Reported duration is one to three months; skin tone: Fitzpatrick IV; the leg is involved; texture is reported as raised or bumpy; the photo was captured at an angle; the patient described the issue as a rash; no relevant systemic symptoms: 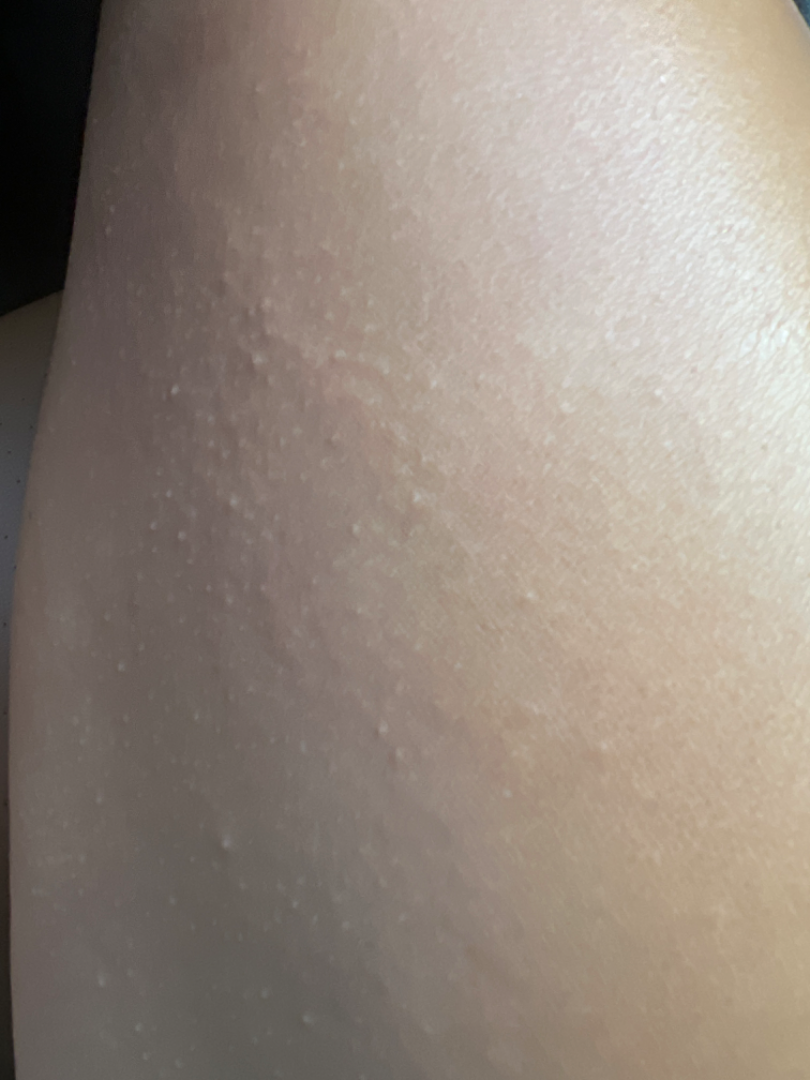On photographic review by a dermatologist: the primary impression is Keratosis pilaris; possibly Lichen nitidus; an alternative is Lichen spinulosus.